A skin lesion imaged with a dermatoscope.
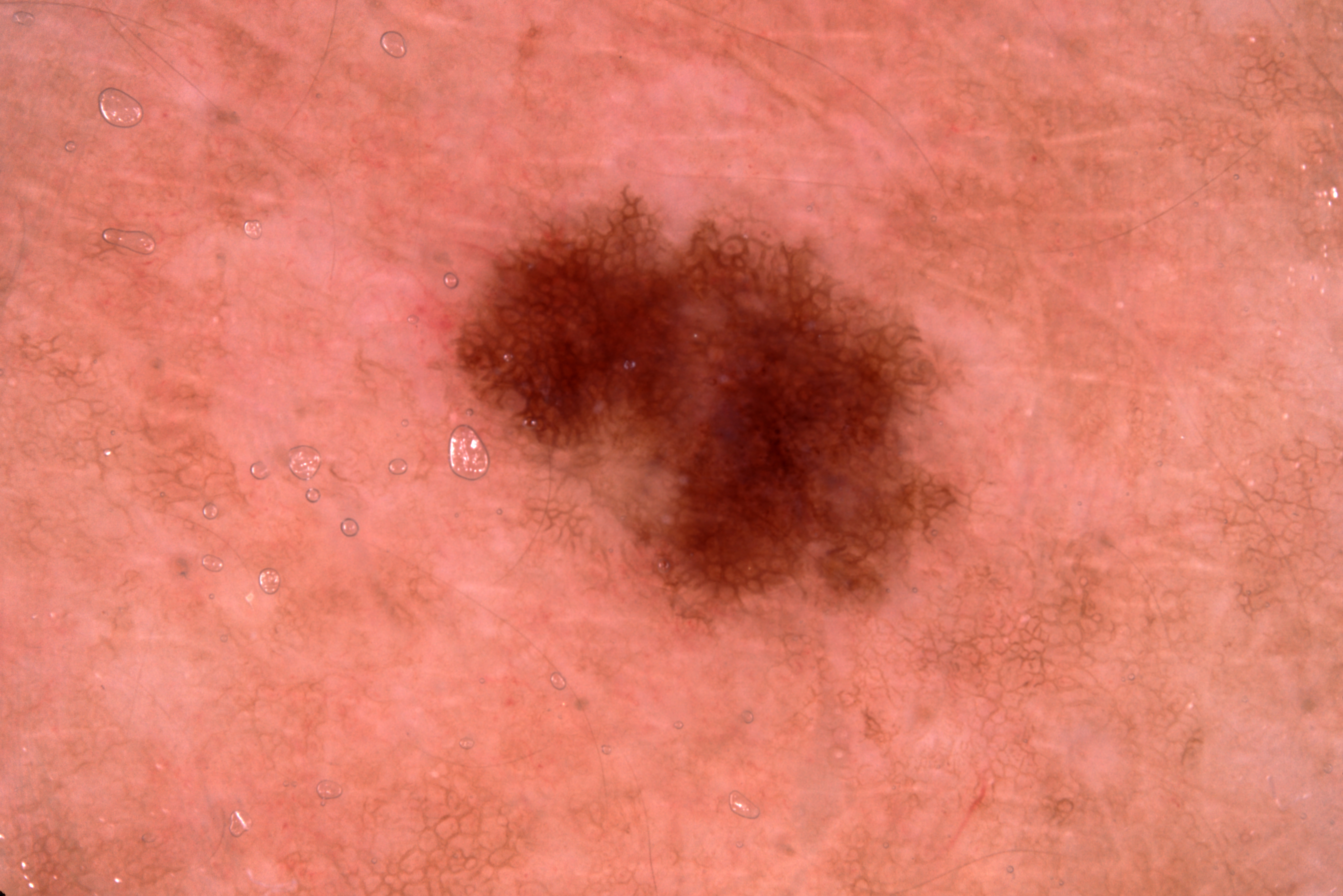• location — 427 183 973 667
• dermoscopic pattern — milia-like cysts and pigment network; absent: streaks and negative network
• diagnostic label — a melanocytic nevus, a benign skin lesion